A female subject, aged 43-47. A dermatoscopic image of a skin lesion.
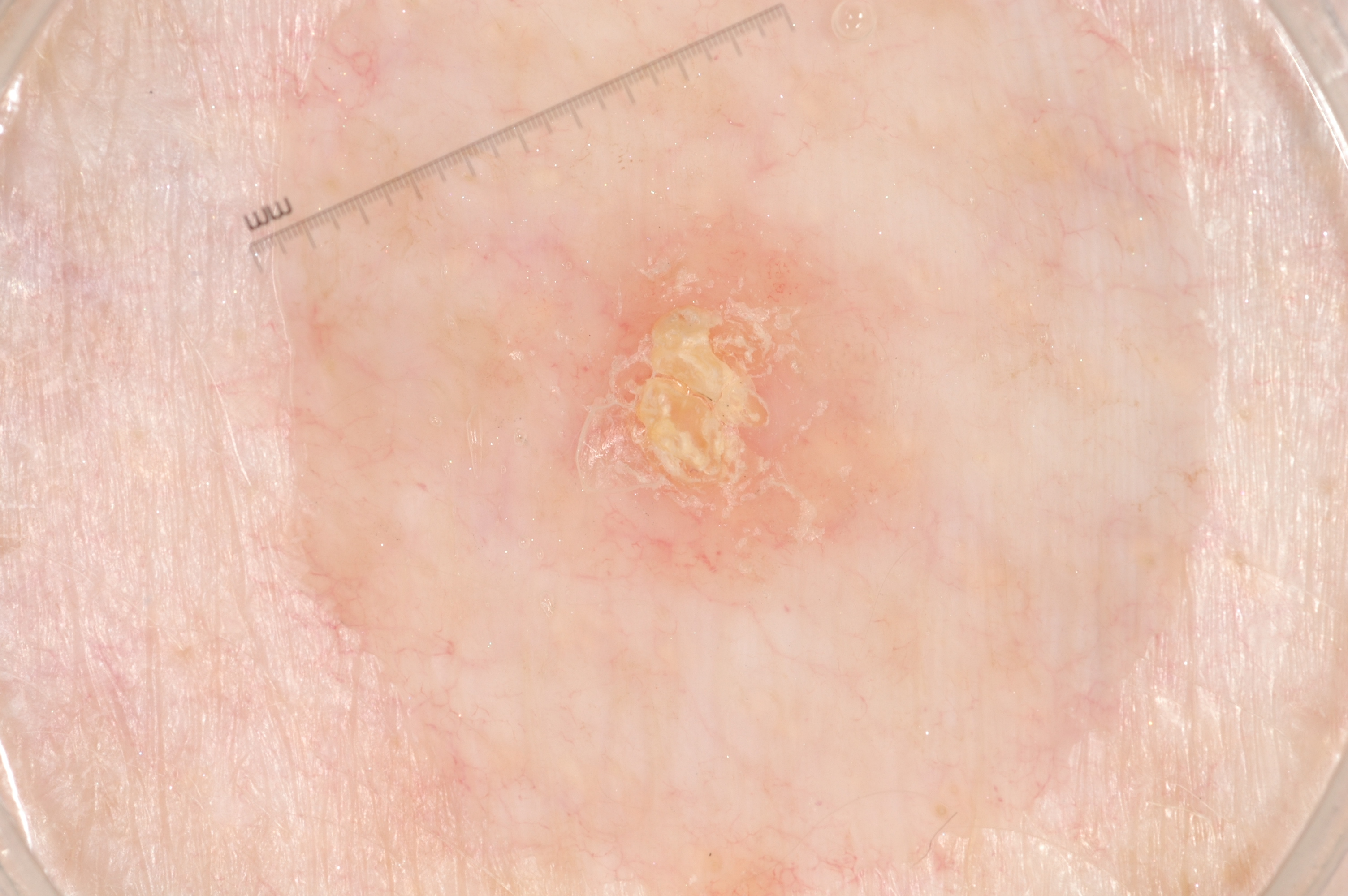The lesion is located at 586 227 925 591. The lesion occupies roughly 8% of the field. Dermoscopically, the lesion shows no milia-like cysts, negative network, pigment network, or streaks. Consistent with a seborrheic keratosis, a benign lesion.